A dermoscopic view of a skin lesion:
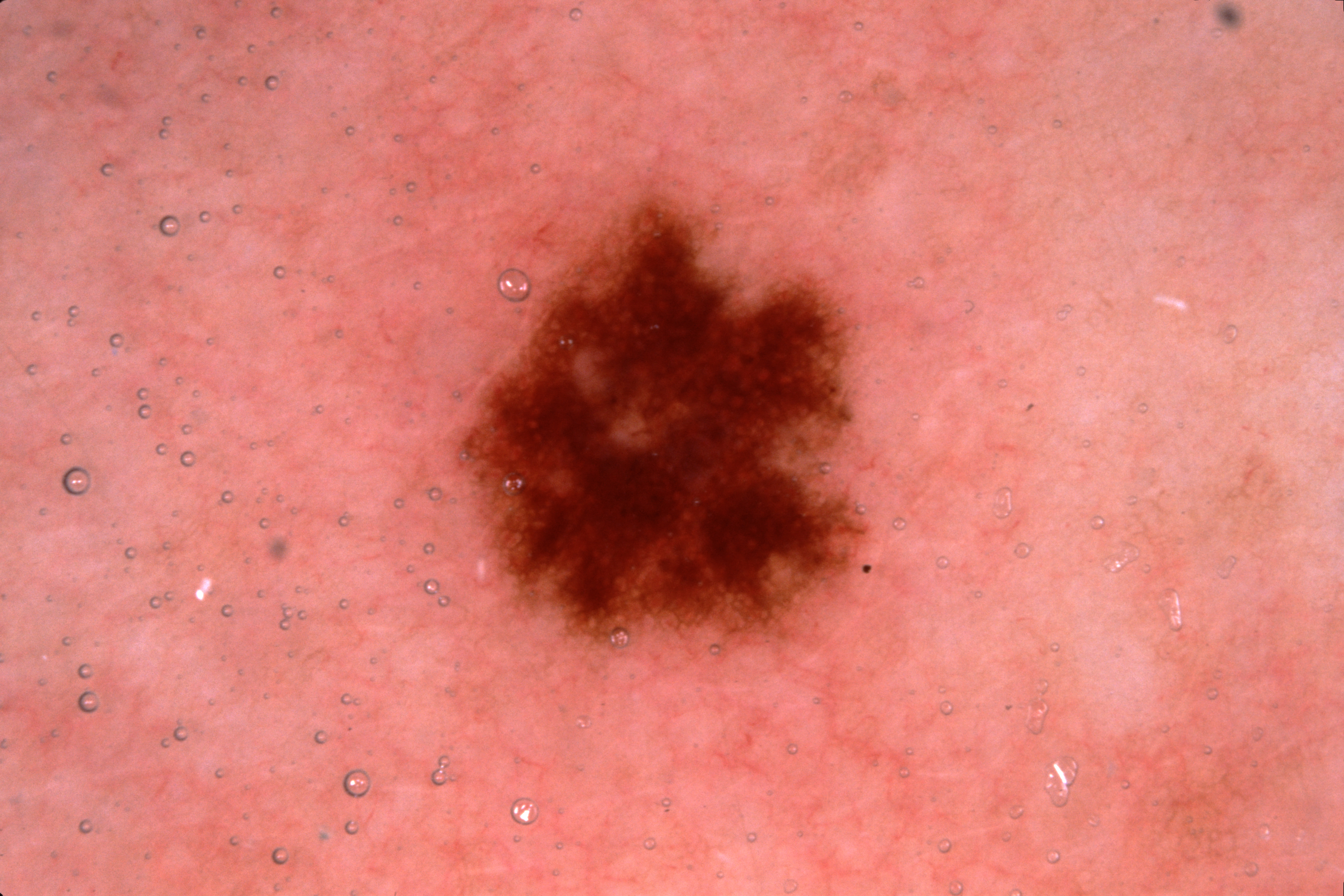The lesion takes up a moderate portion of the field.
With coordinates (x1, y1, x2, y2), the lesion's extent is 454/181/866/651.
The dermoscopic pattern shows pigment network, with no milia-like cysts, streaks, or negative network.
Clinically diagnosed as a melanocytic nevus, a benign lesion.